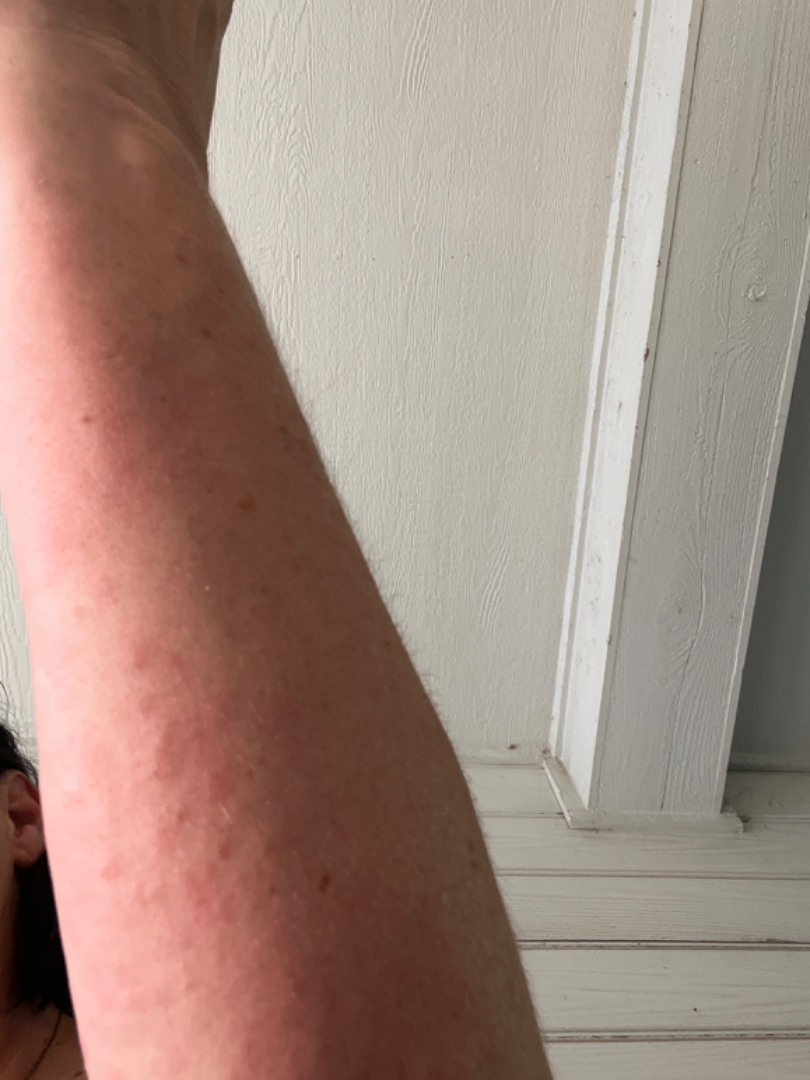subject=female, age 50–59
body site=arm
view=at an angle
differential diagnosis=Urticaria, Eczema and Allergic Contact Dermatitis were considered with similar weight